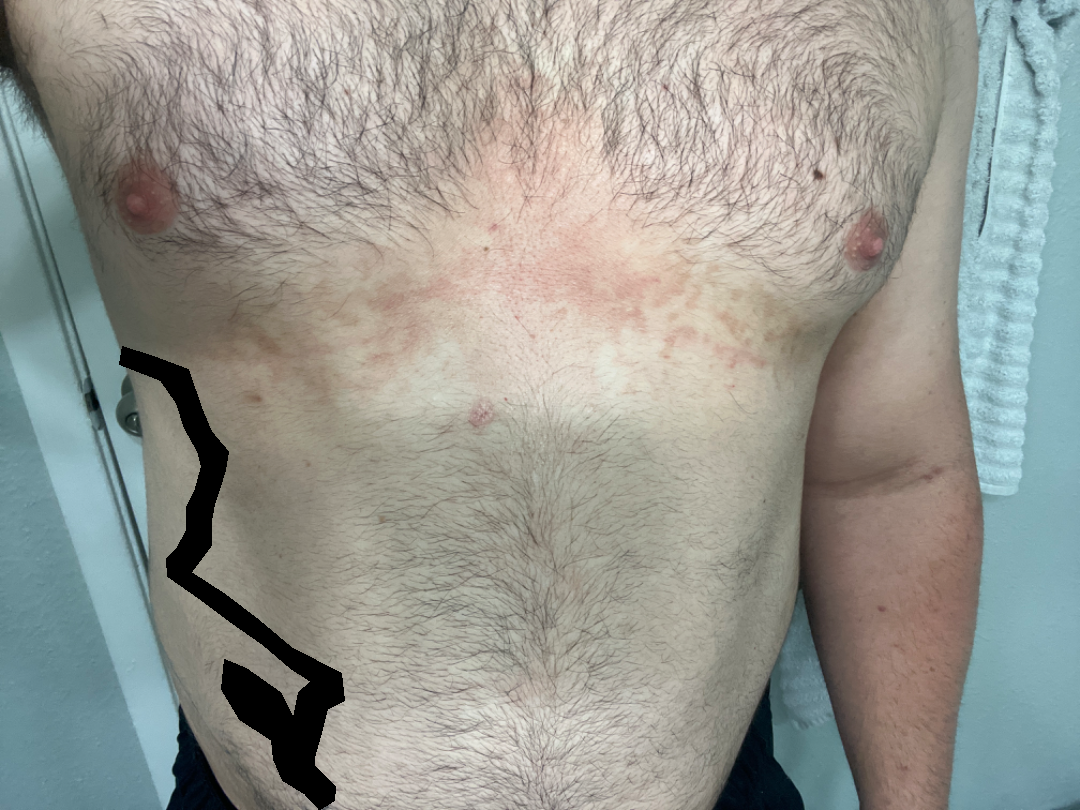The subject is 30–39, male. The patient also reports fatigue. The photograph was taken at an angle. The patient indicates the condition has been present for more than five years. The patient described the issue as a rash. The patient indicates the lesion is flat and rough or flaky. The lesion is associated with enlargement, bothersome appearance and itching. On remote dermatologist review: Confluent and reticulate papillomatosis (leading).